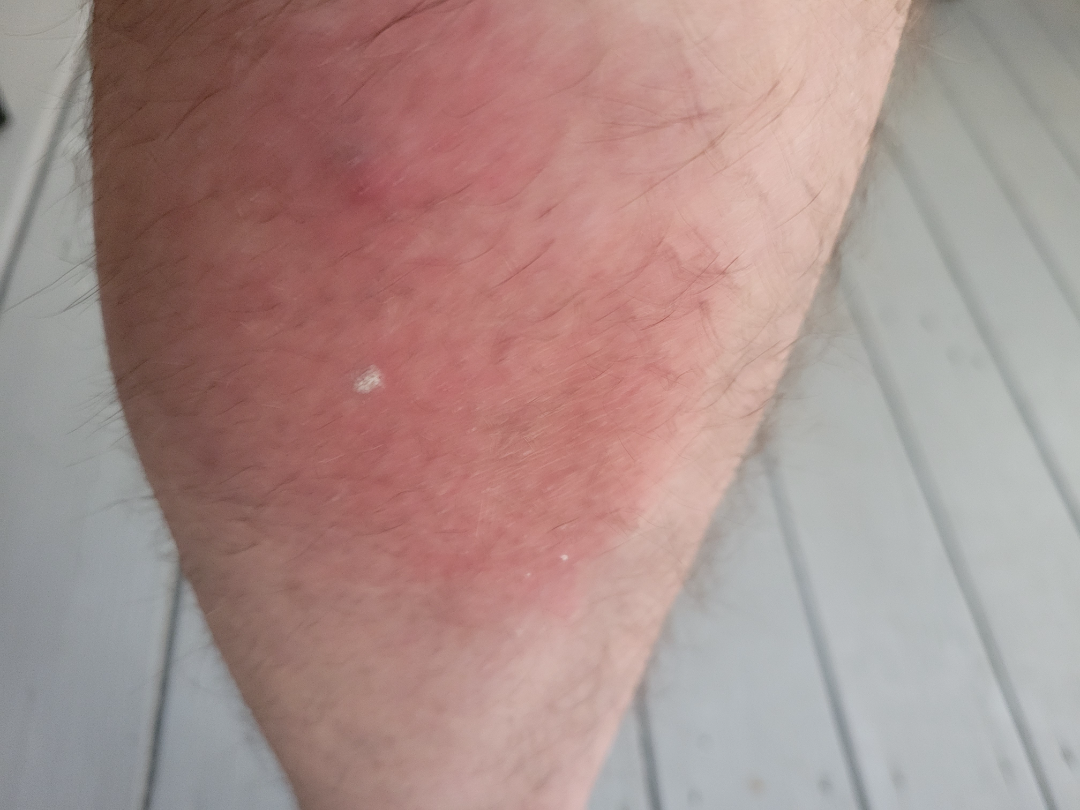Patient information:
The patient reports pain. Located on the leg. The condition has been present for three to twelve months. Skin tone: Fitzpatrick skin type I. The patient reports the lesion is raised or bumpy. An image taken at an angle. No relevant systemic symptoms.
Review:
On teledermatology review, the leading consideration is Cellulitis; also on the differential is Eczema; also consider Necrobiosis lipoidica.